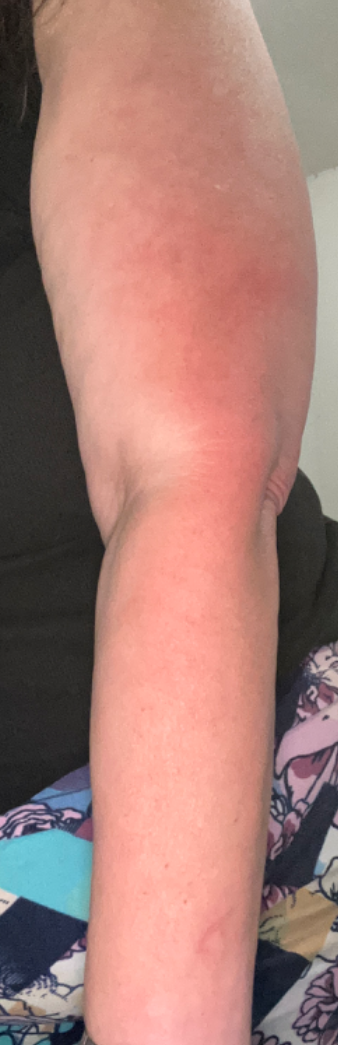{"patient": "female, age 40–49", "texture": "raised or bumpy", "symptoms": "burning", "patient_category": "a rash", "shot_type": "at a distance", "duration": "about one day", "body_site": "arm", "differential": "Photodermatitis"}